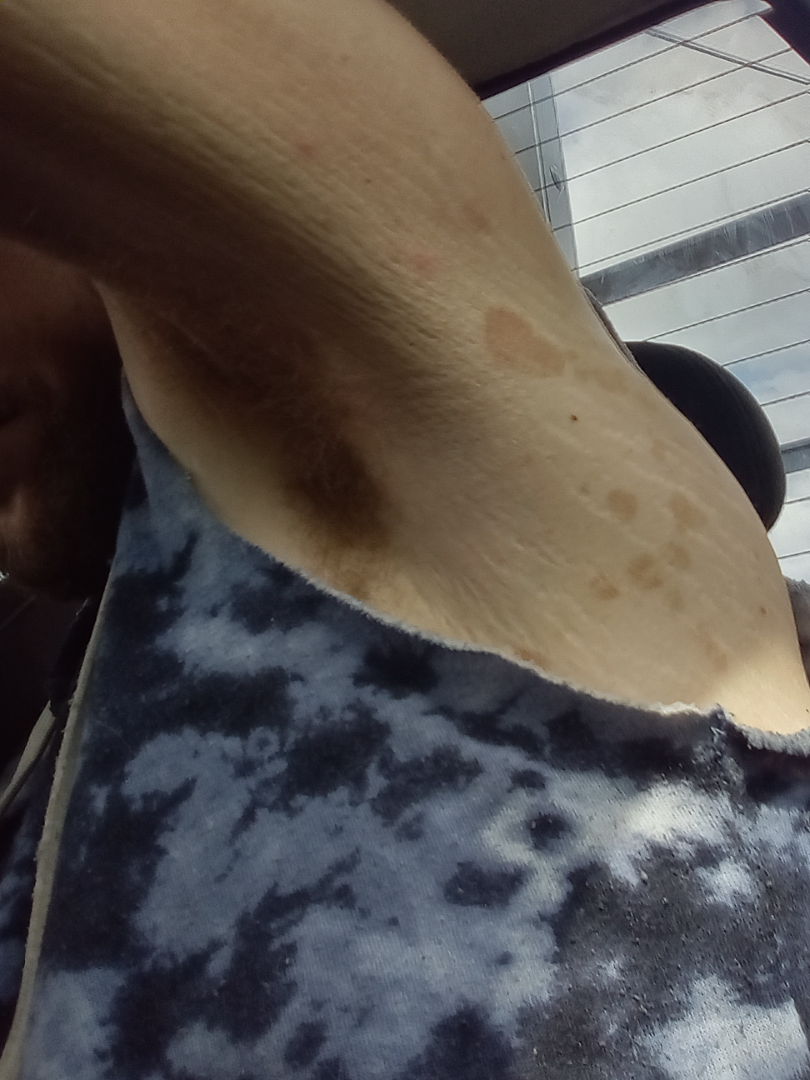Assessment:
The skin condition could not be confidently assessed from this image.